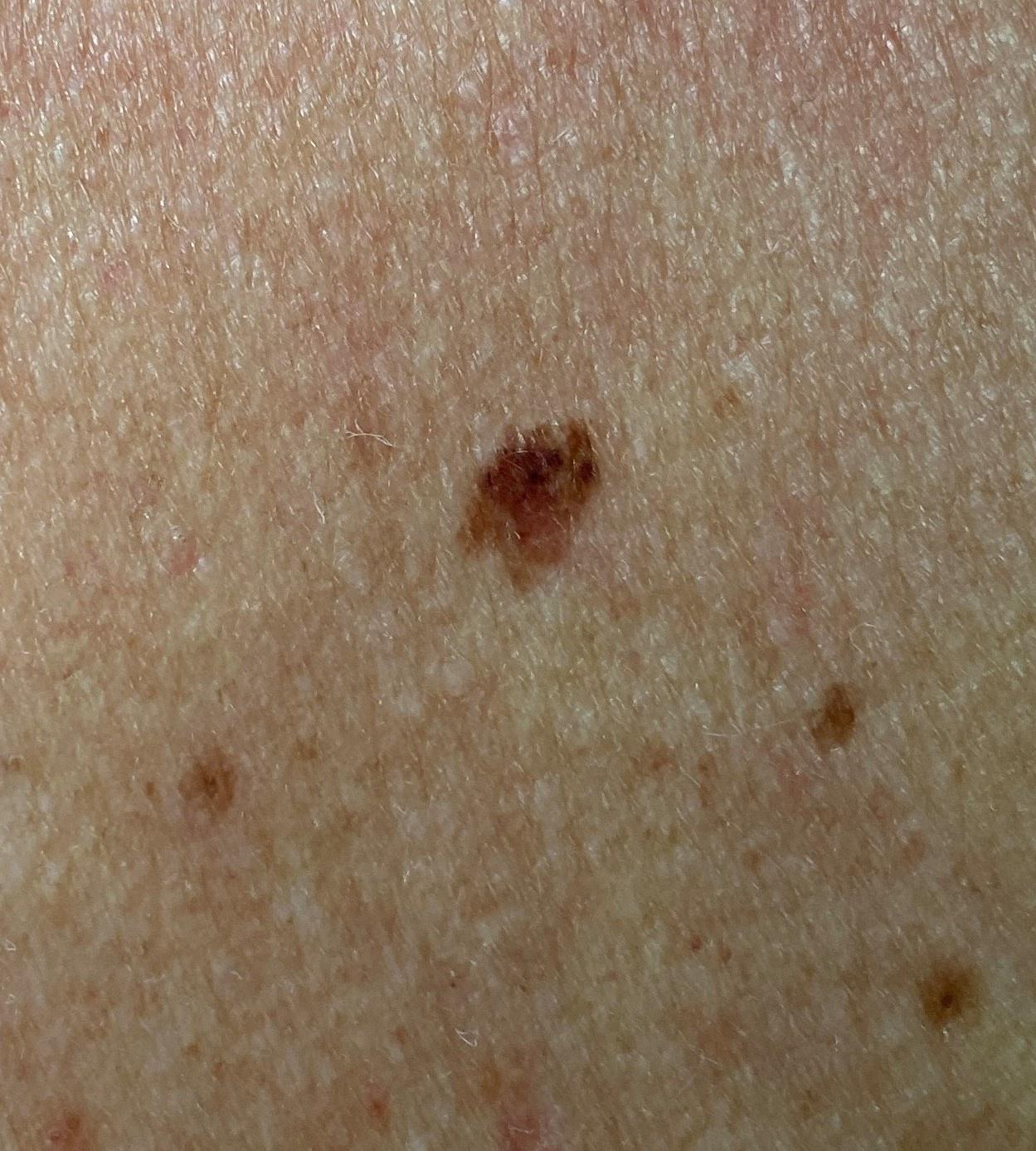<skin_lesion>
  <diagnosis>
    <name>Nevus</name>
    <malignancy>benign</malignancy>
    <confirmation>histopathology</confirmation>
    <lineage>melanocytic</lineage>
  </diagnosis>
</skin_lesion>